Present for less than one week · the photo was captured at an angle · the arm is involved · the patient considered this acne · no associated systemic symptoms reported · the contributor is a female aged 18–29:
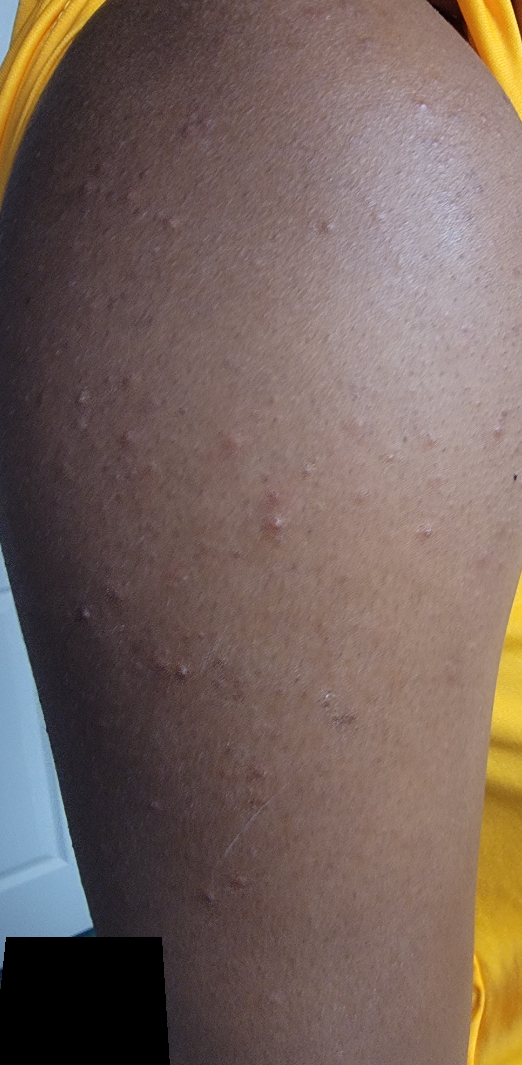Favoring Keratosis pilaris.